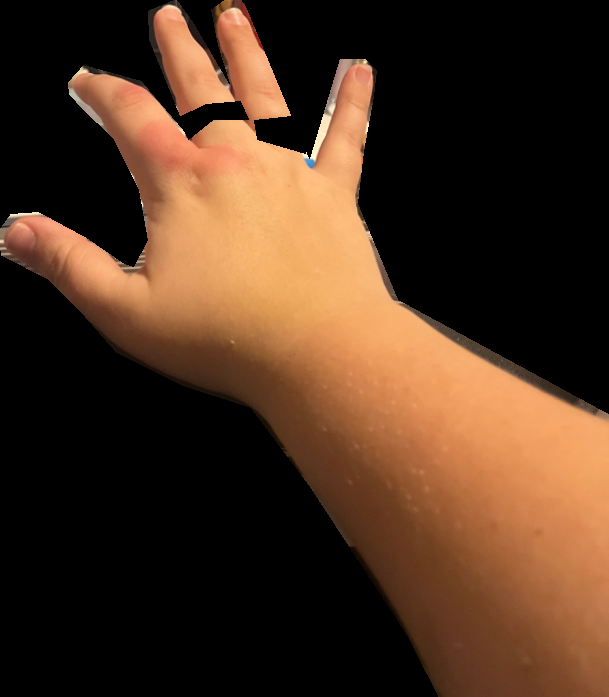systemic_symptoms: fatigue
duration: about one day
patient: female, age 18–29
symptoms:
  - enlargement
  - burning
texture: raised or bumpy
body_site: back of the hand
shot_type: at a distance
differential:
  Urticaria: 0.41
  Insect Bite: 0.41
  Cellulitis: 0.18